The photograph is a close-up of the affected area:
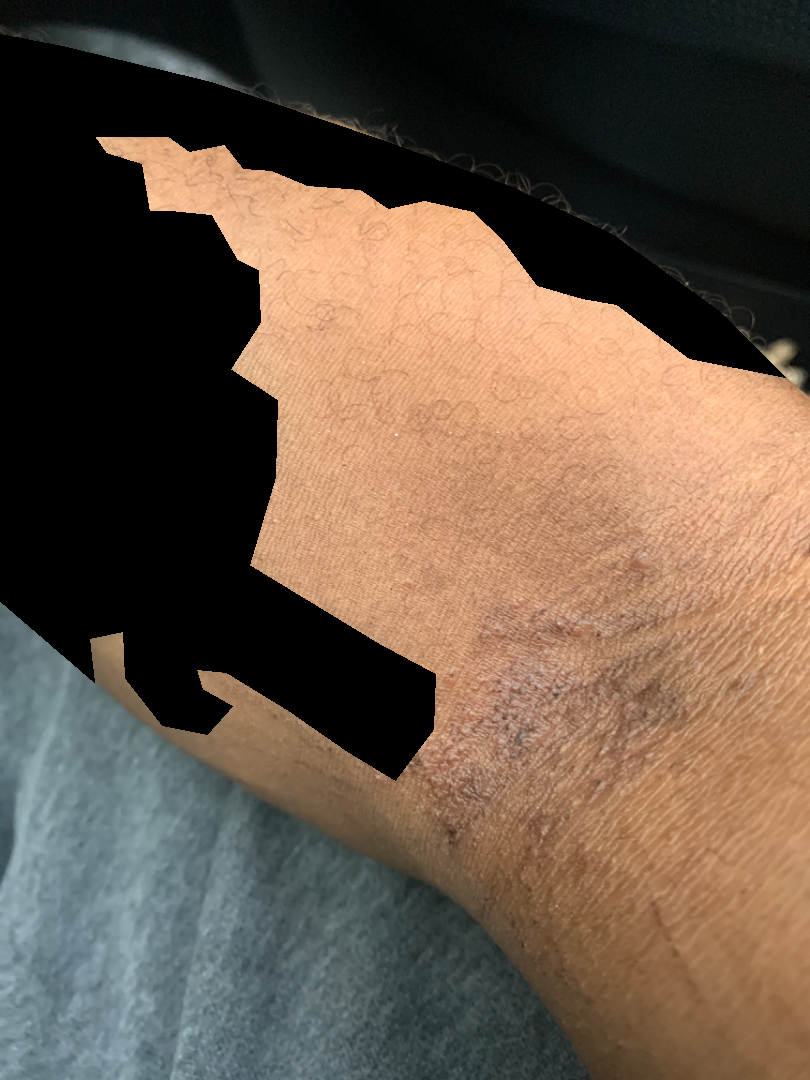Q: What is the differential diagnosis?
A: favoring Eczema; also on the differential is Chronic dermatitis, NOS